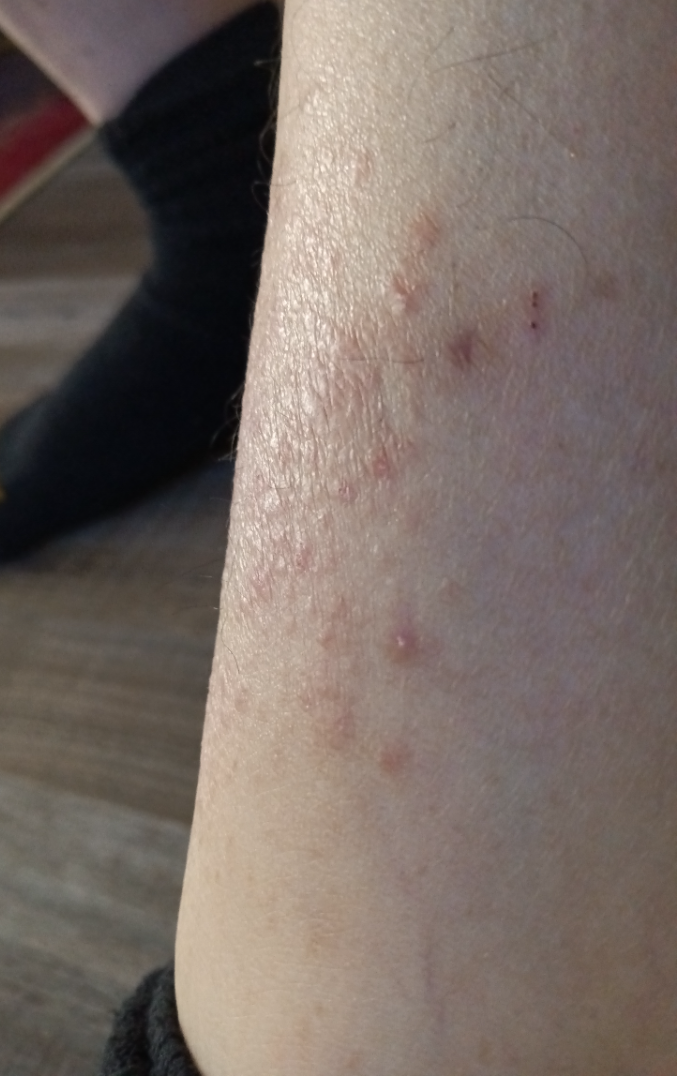An image taken at an angle.
The affected area is the leg.
The lesion is described as raised or bumpy.
Reviewed remotely by one dermatologist: the impression is Eczema.